The patient was assessed as Fitzpatrick skin type III; a male subject in their 70s; a clinical close-up photograph of a skin lesion; the chart records tobacco use, alcohol use, pesticide exposure, prior malignancy (patient or family), and prior skin cancer (patient or family).
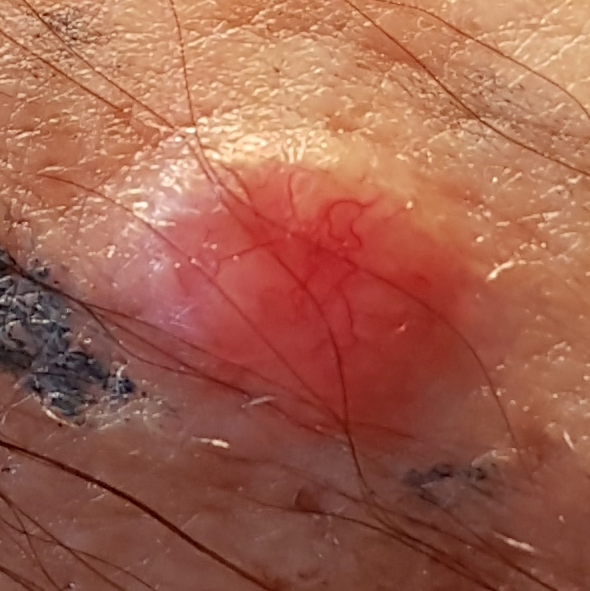site = an arm | diameter = 9x7 mm | patient-reported symptoms = growth, elevation, itching | diagnosis = basal cell carcinoma (biopsy-proven).